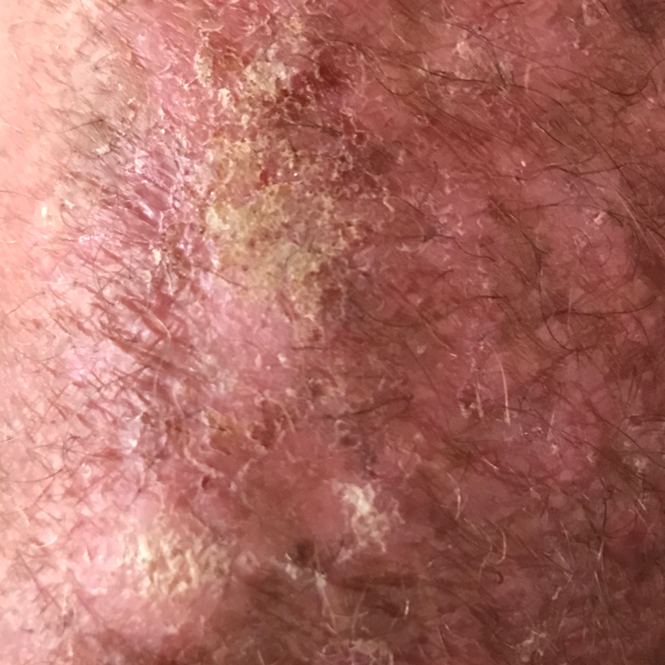imaging = smartphone clinical photo; anatomic site = a forearm; impression = actinic keratosis (clinical consensus).